A clinical photo of a skin lesion taken with a smartphone. A subject age 36.
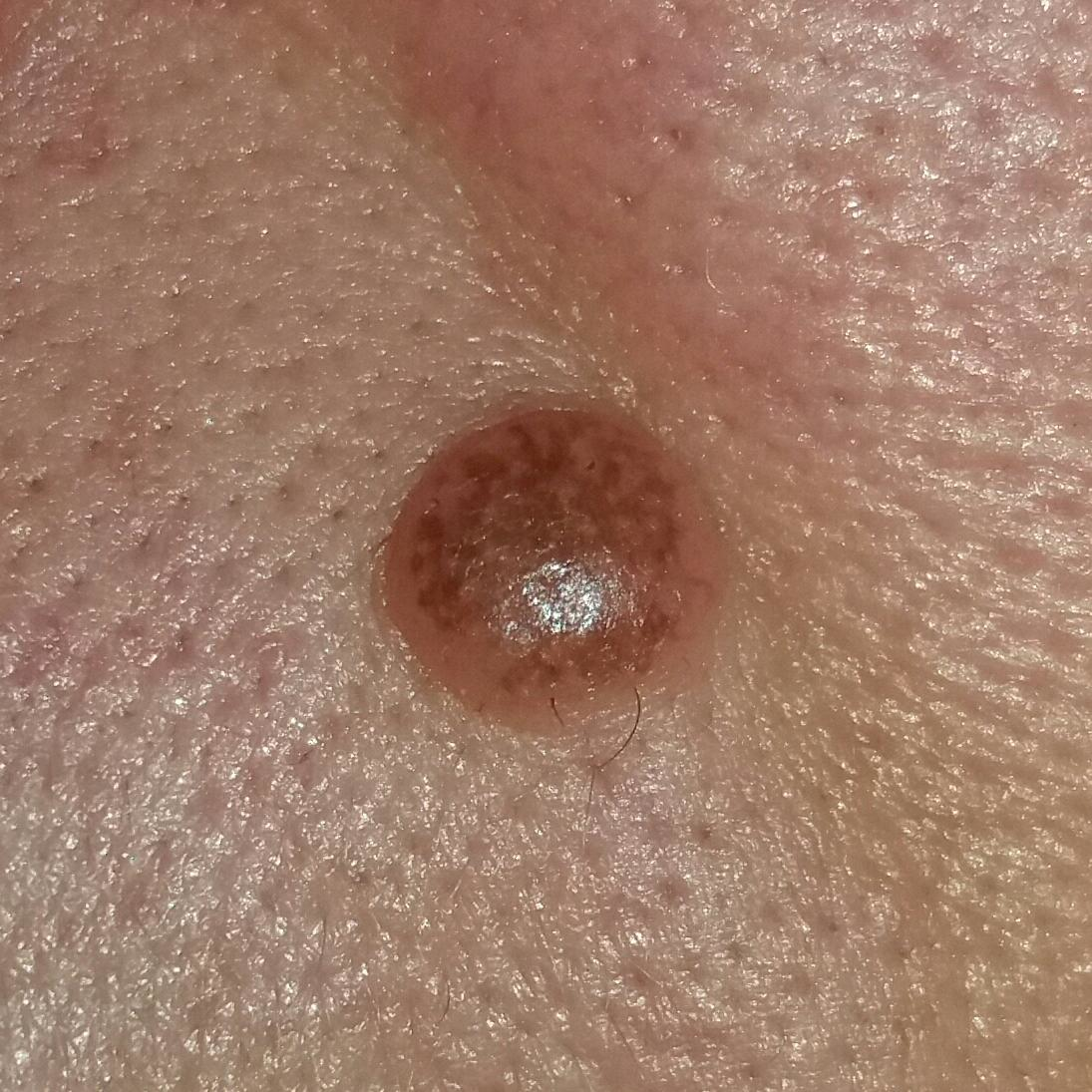Located on a lip. The patient reports that the lesion has grown and is elevated. Expert review favored a nevus.